The patient is Fitzpatrick phototype II; history notes pesticide exposure; a male patient 62 years old; a smartphone photograph of a skin lesion.
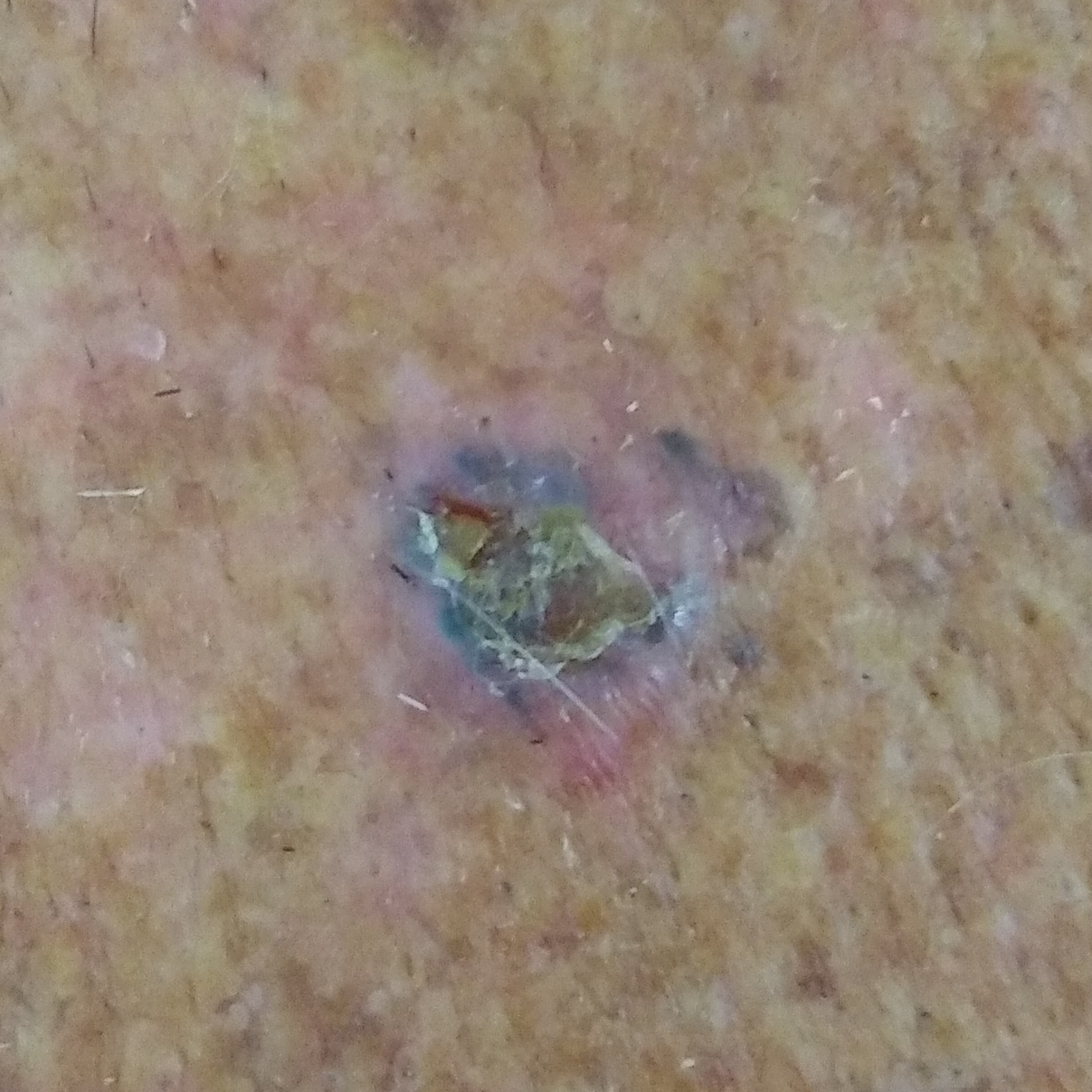{
  "lesion_location": "the chest",
  "lesion_size": {
    "diameter_1_mm": 1.2,
    "diameter_2_mm": 1.2
  },
  "symptoms": {
    "present": [
      "bleeding",
      "elevation",
      "pain",
      "itching"
    ]
  },
  "diagnosis": {
    "name": "basal cell carcinoma",
    "code": "BCC",
    "malignancy": "malignant",
    "confirmation": "histopathology"
  }
}